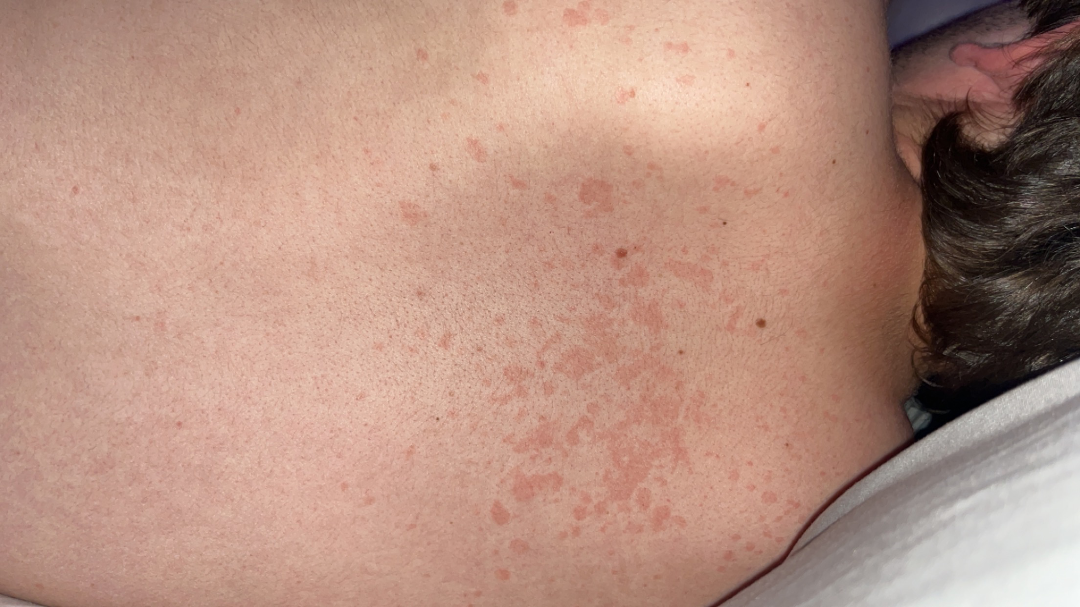Assessment: On remote review of the image: most consistent with Tinea Versicolor.